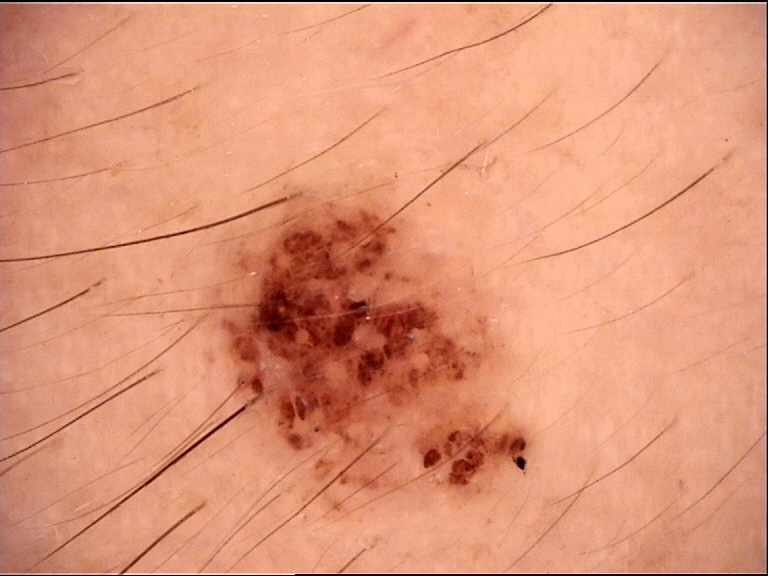Impression:
The diagnosis was a compound nevus.